Dermoscopy of a skin lesion: 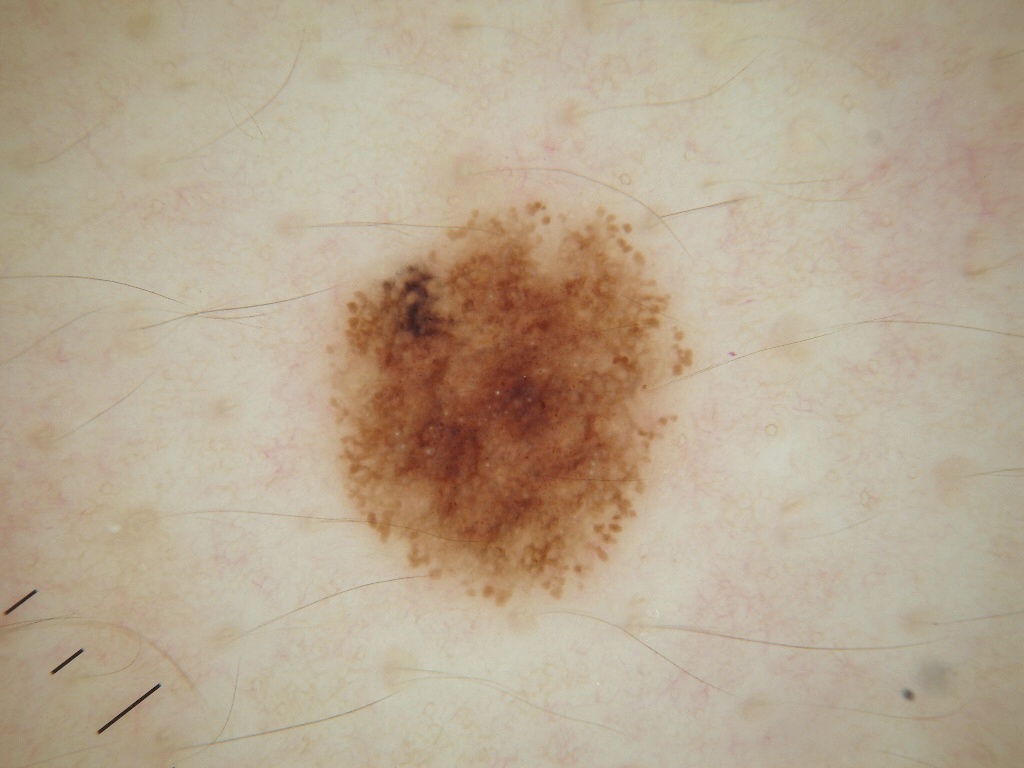dermoscopic findings=milia-like cysts and pigment network; absent: negative network, globules, and streaks
bounding box=[324,193,690,604]
diagnostic label=a melanocytic nevus, a benign skin lesion